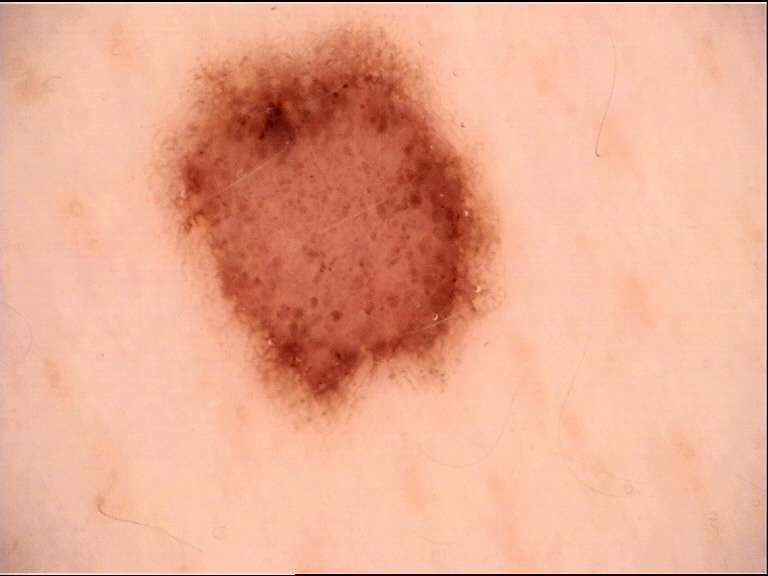{
  "image": "dermatoscopy",
  "diagnosis": {
    "name": "dysplastic junctional nevus",
    "code": "jd",
    "malignancy": "benign",
    "super_class": "melanocytic",
    "confirmation": "expert consensus"
  }
}